This image was taken at a distance, located on the leg — 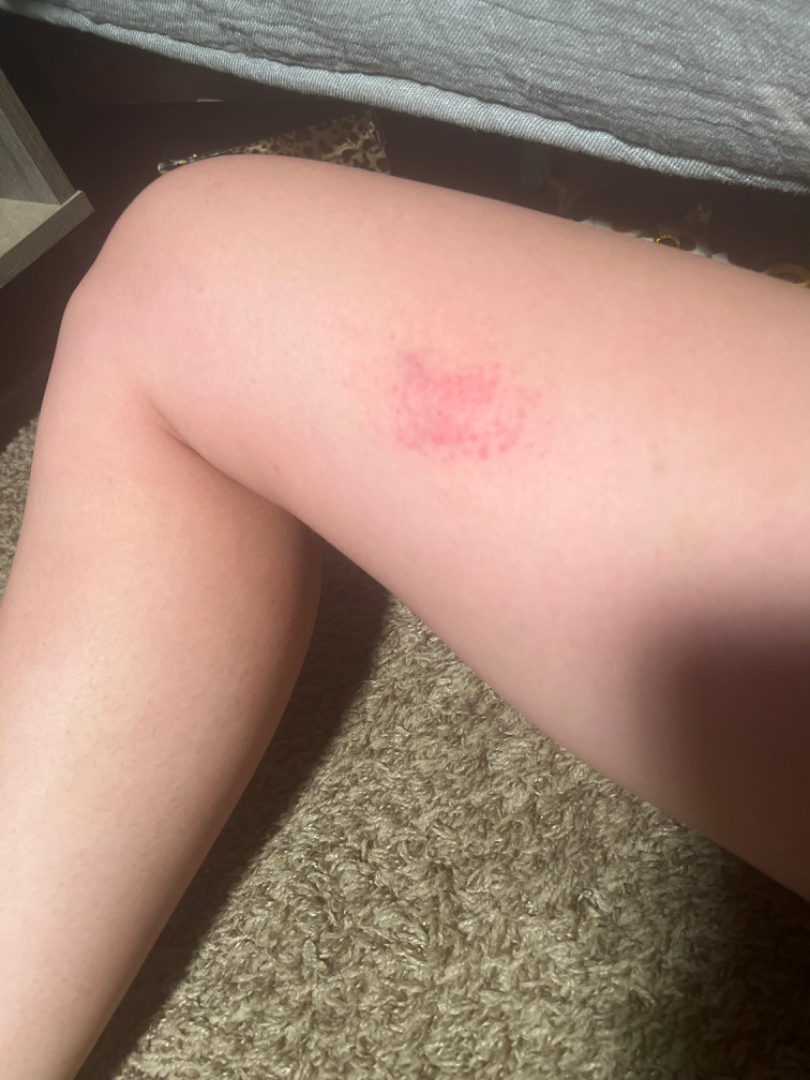Assessment: The reviewer was unable to grade this case for skin condition.